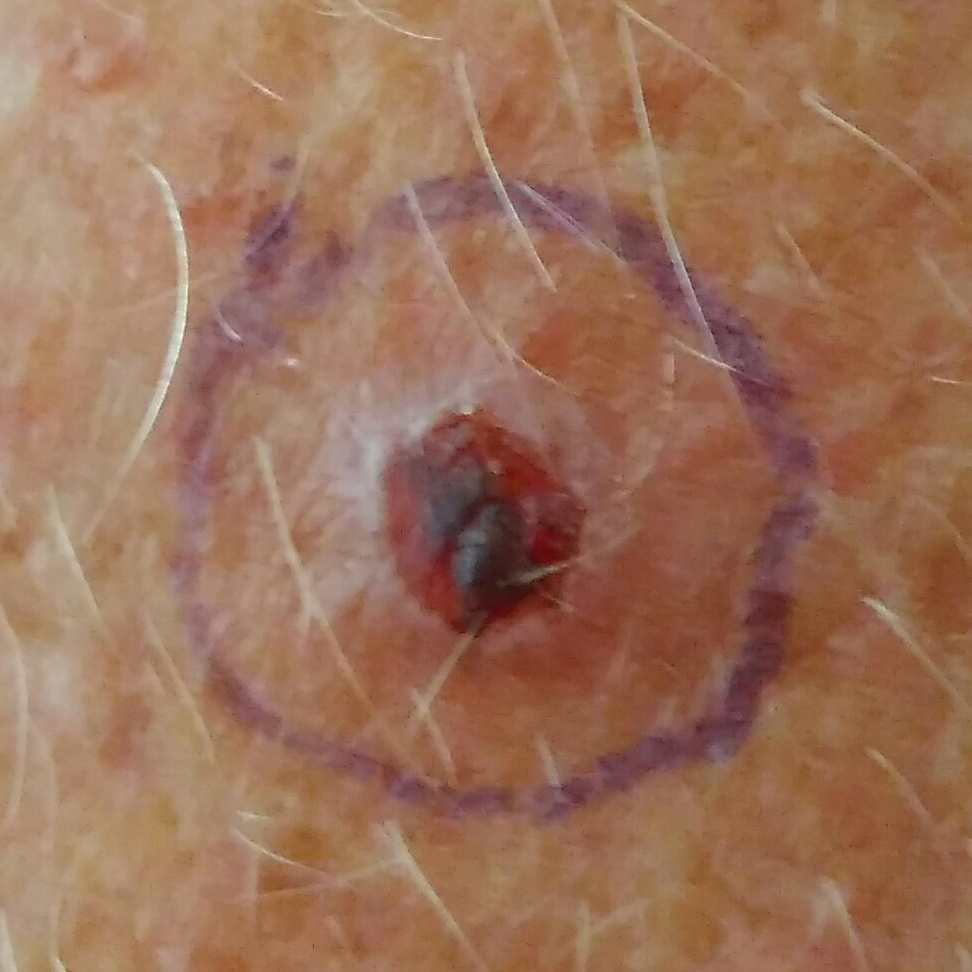Q: What is the imaging modality?
A: clinical photograph
Q: What is the patient's skin type?
A: II
Q: Patient demographics?
A: female, in their 60s
Q: What is the anatomic site?
A: a forearm
Q: Lesion size?
A: 7x6 mm
Q: Any reported symptoms?
A: growth, pain, itching, bleeding, elevation
Q: What did the workup show?
A: basal cell carcinoma (biopsy-proven)